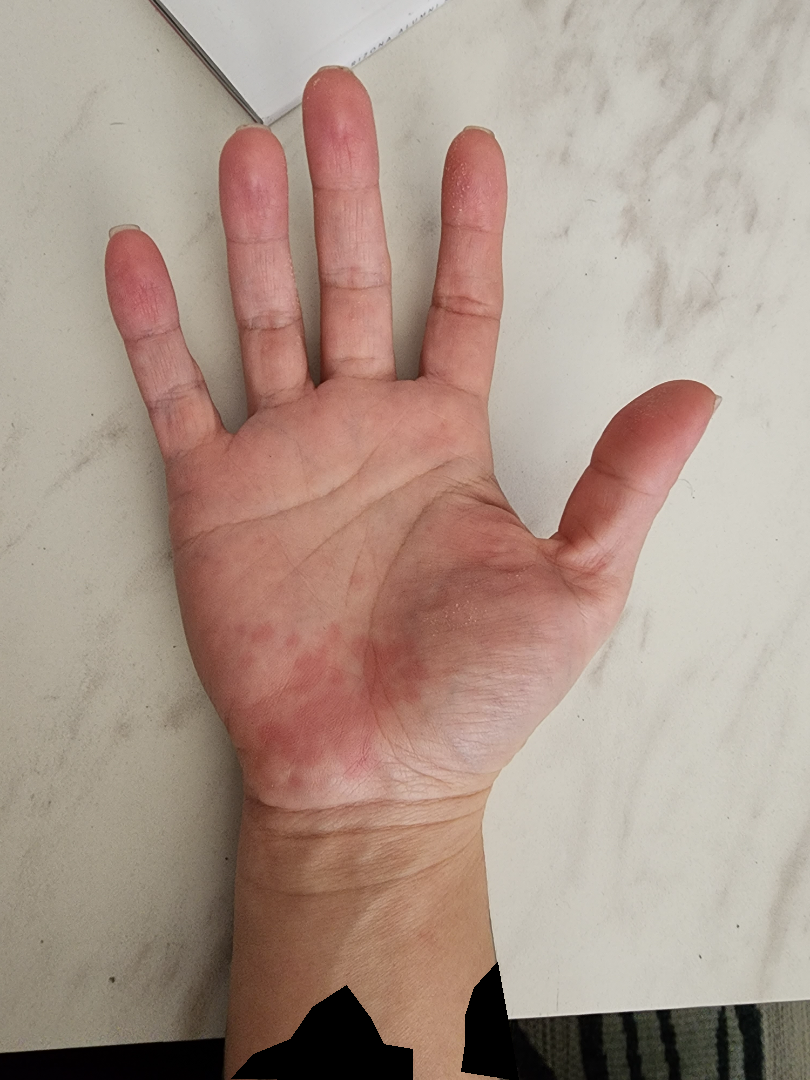{"body_site": "palm", "texture": "flat", "patient_category": "a rash", "symptoms": "itching", "duration": "about one day", "shot_type": "close-up", "differential": {"leading": ["Allergic Contact Dermatitis"], "considered": ["Psoriasis", "Insect Bite"]}}